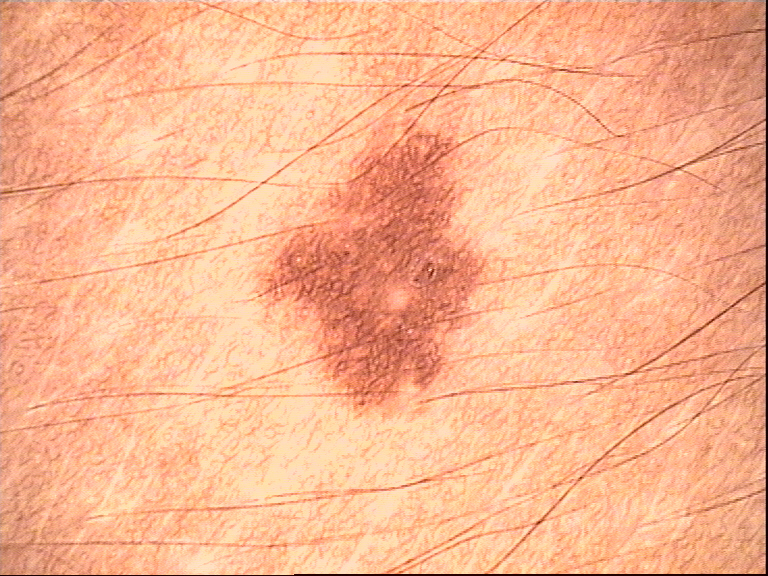diagnosis=dysplastic junctional nevus (expert consensus)